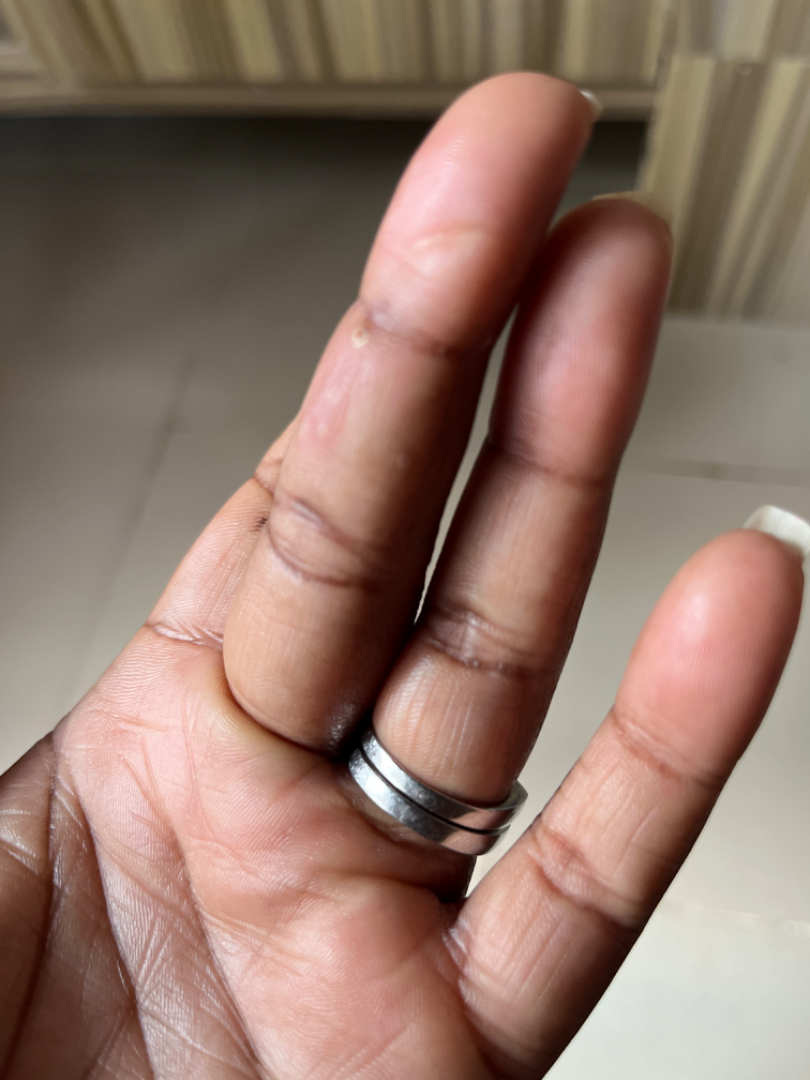surface texture=raised or bumpy; body site=palm; other reported symptoms=none reported; patient's own categorization=a rash; duration=less than one week; framing=at an angle; contributor=female, age 18–29; patient-reported symptoms=enlargement, bothersome appearance and pain; clinical impression=Impetigo and Foreign body were each considered, in no particular order.